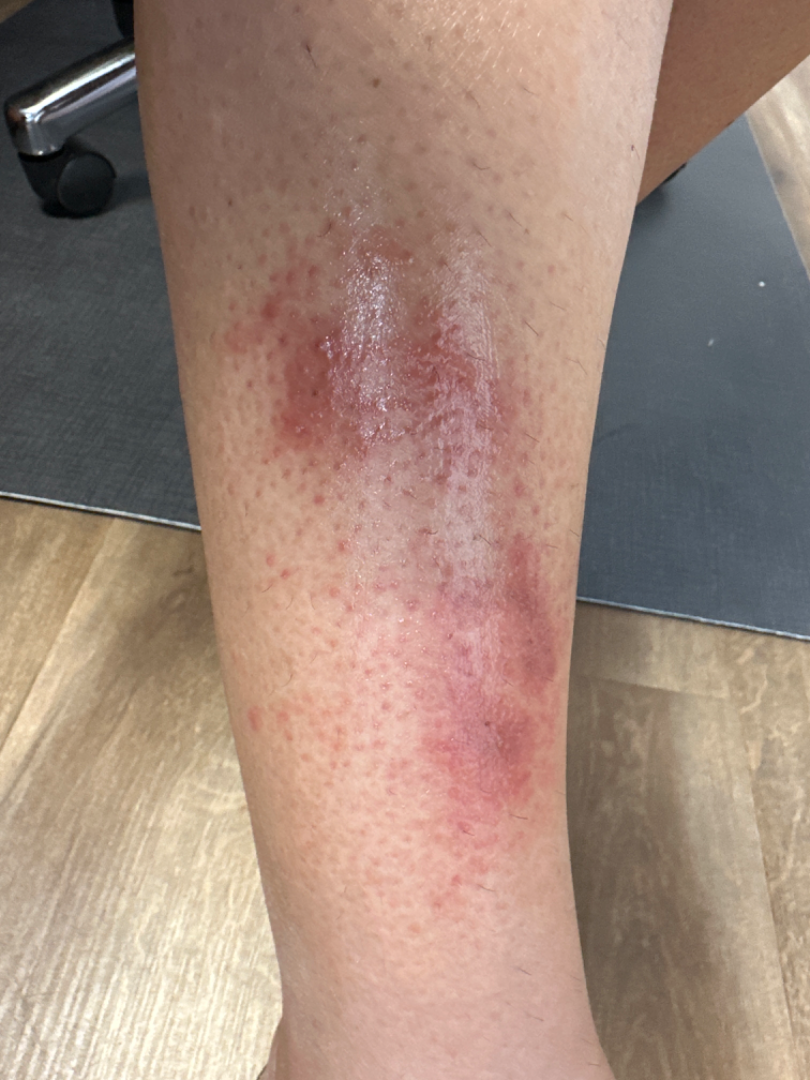Review: The condition could not be reliably identified from the image.